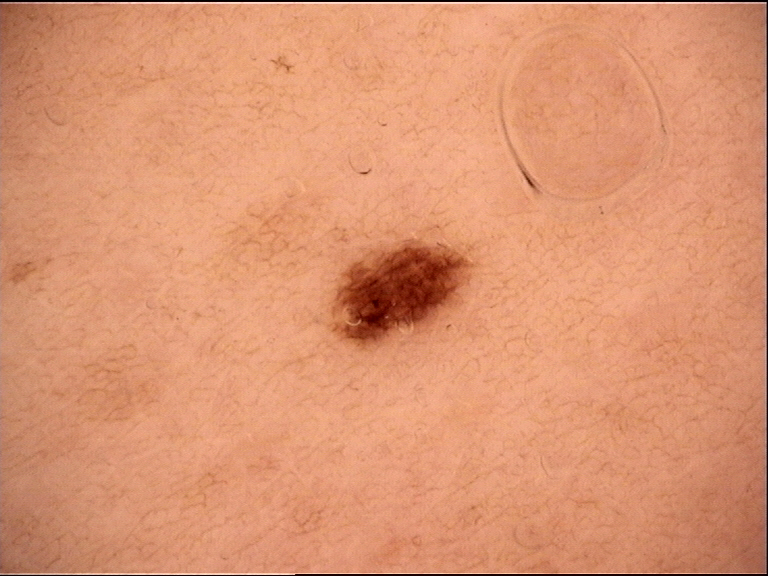Q: What kind of image is this?
A: dermatoscopy
Q: What is the diagnosis?
A: dysplastic junctional nevus (expert consensus)